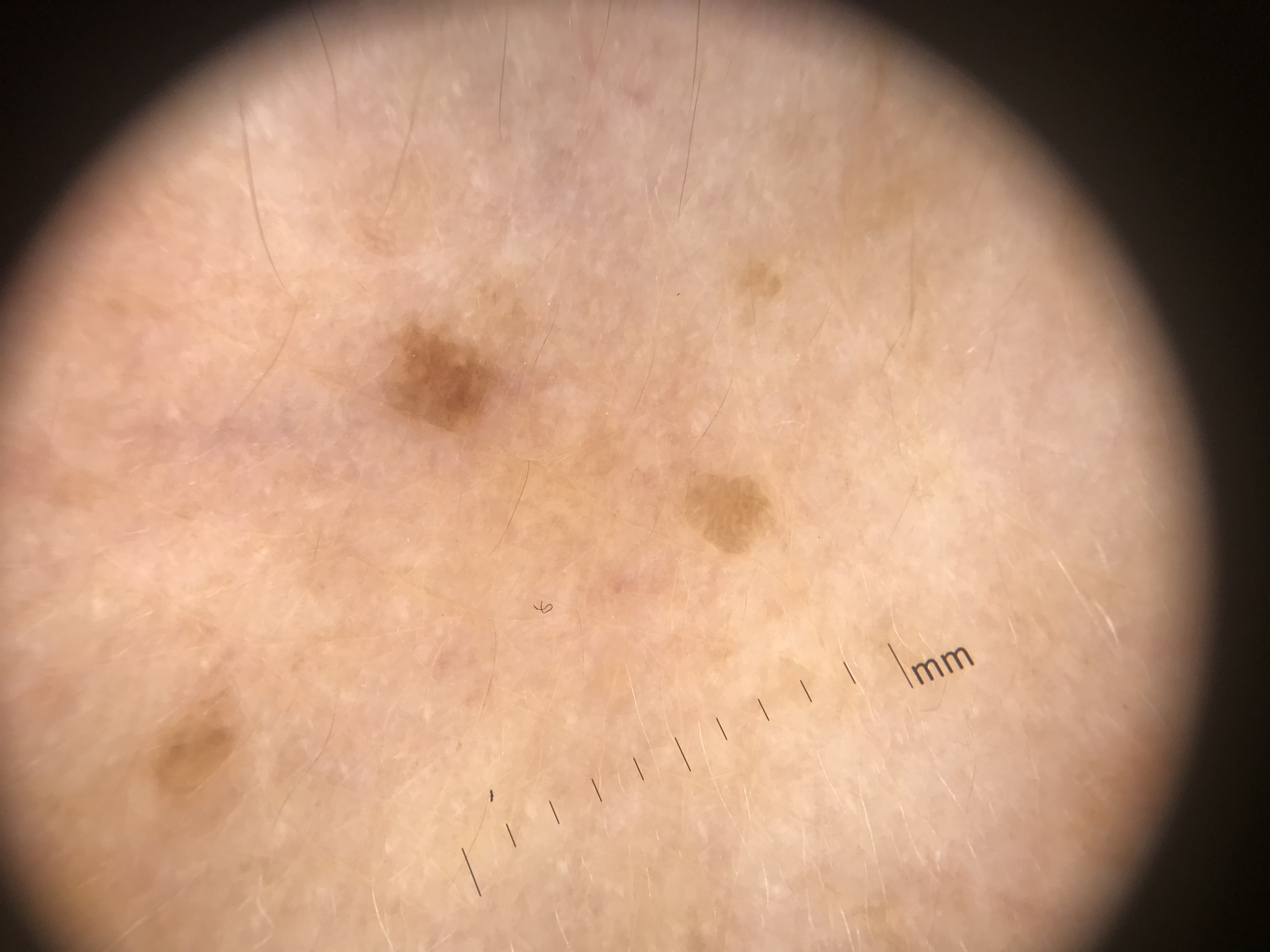The diagnosis was a seborrheic keratosis.